Female contributor, age 30–39; an image taken at an angle; the arm and leg are involved — 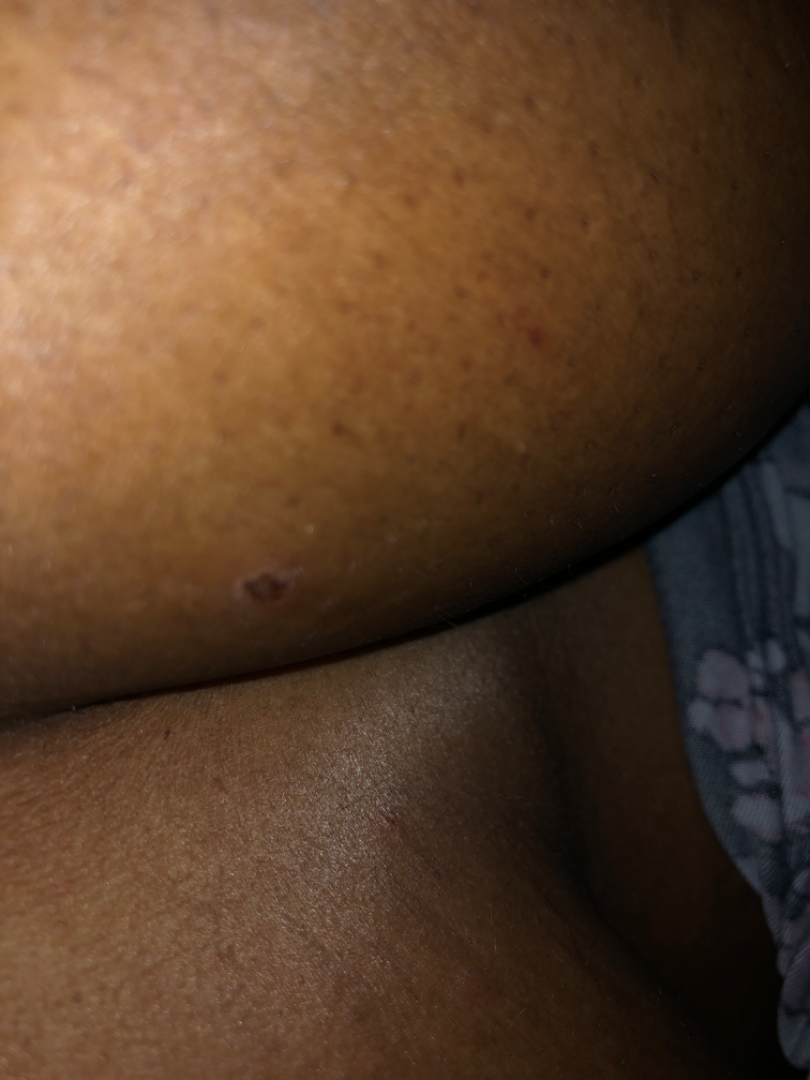• assessment — indeterminate
• reported symptoms — itching
• symptom duration — less than one week
• skin tone — Fitzpatrick skin type IV; human graders estimated Monk skin tone scale 5 or 6 (two reviewer pools)
• texture — raised or bumpy
• self-categorized as — a rash